The affected area is the arm. An image taken at an angle — 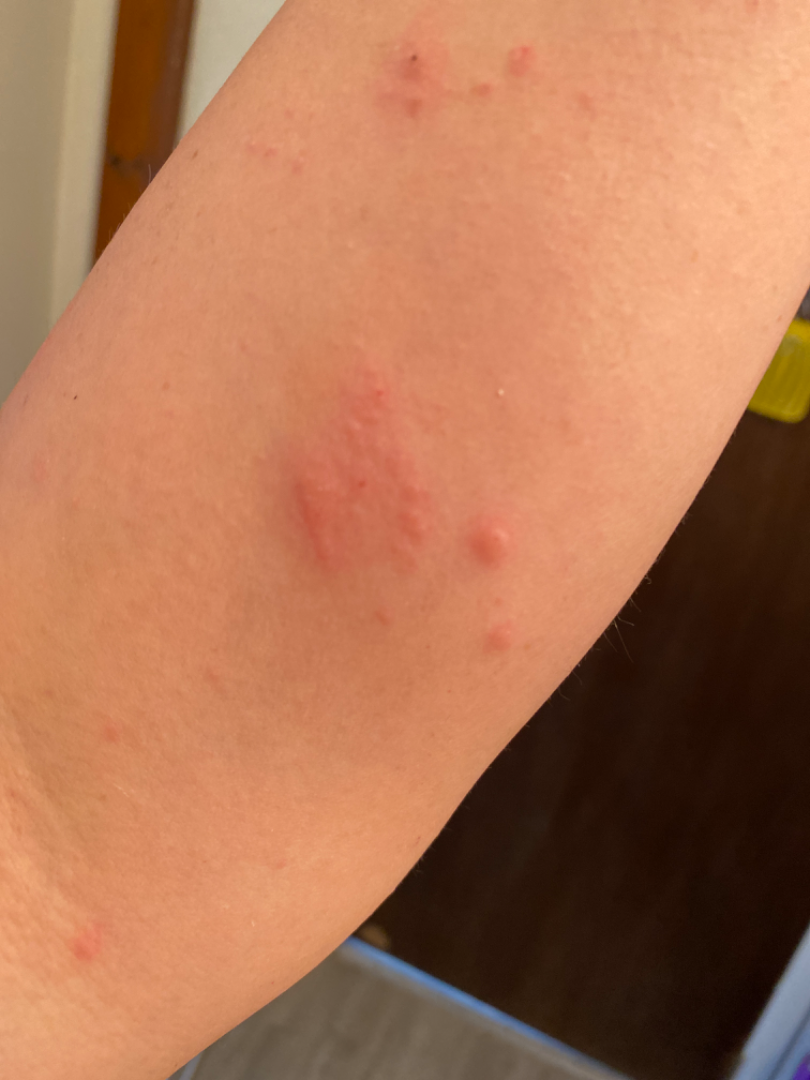differential:
  leading:
    - Allergic Contact Dermatitis
  considered:
    - Herpes Zoster
    - Eczema